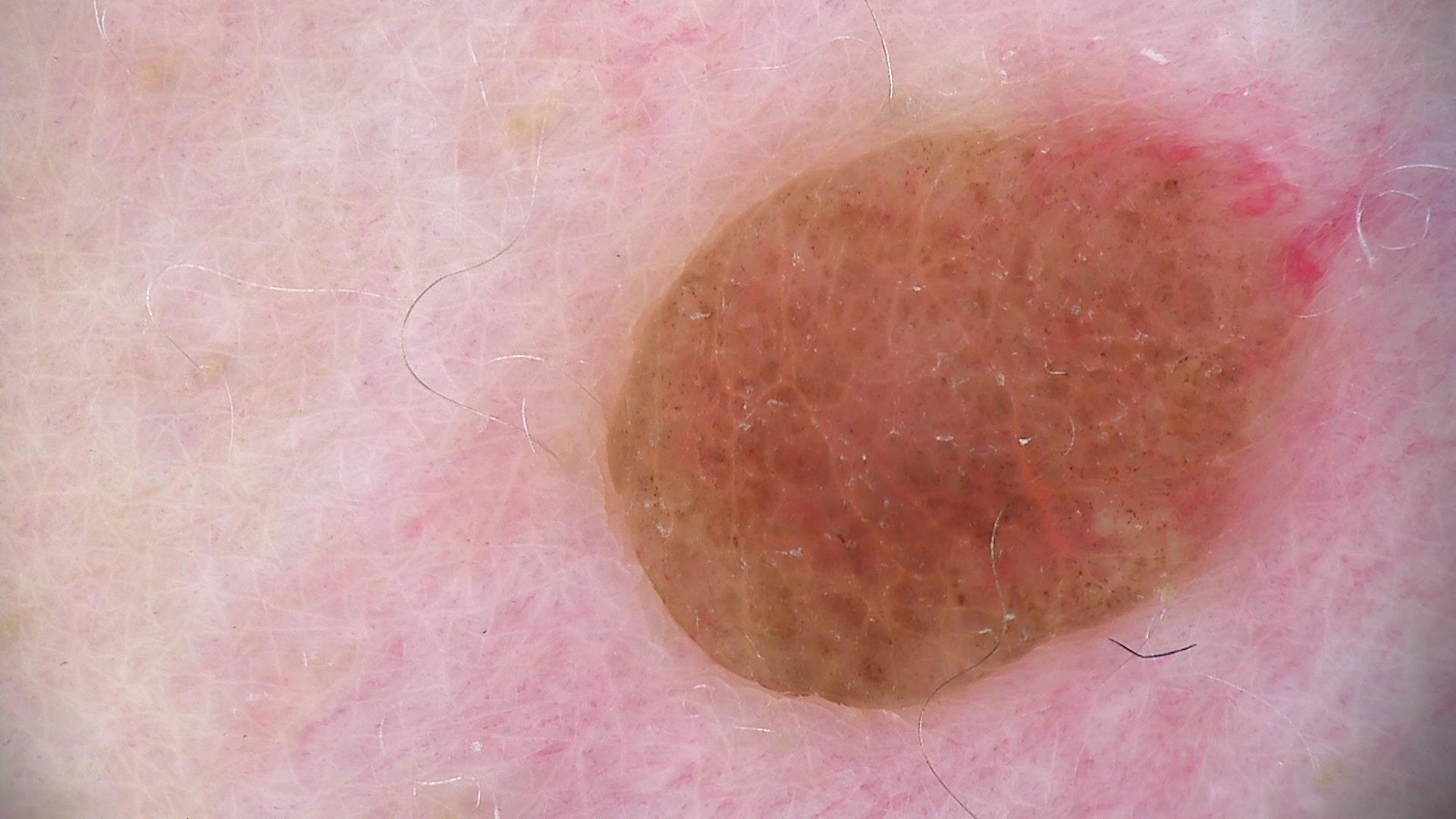class = dermal nevus (expert consensus).